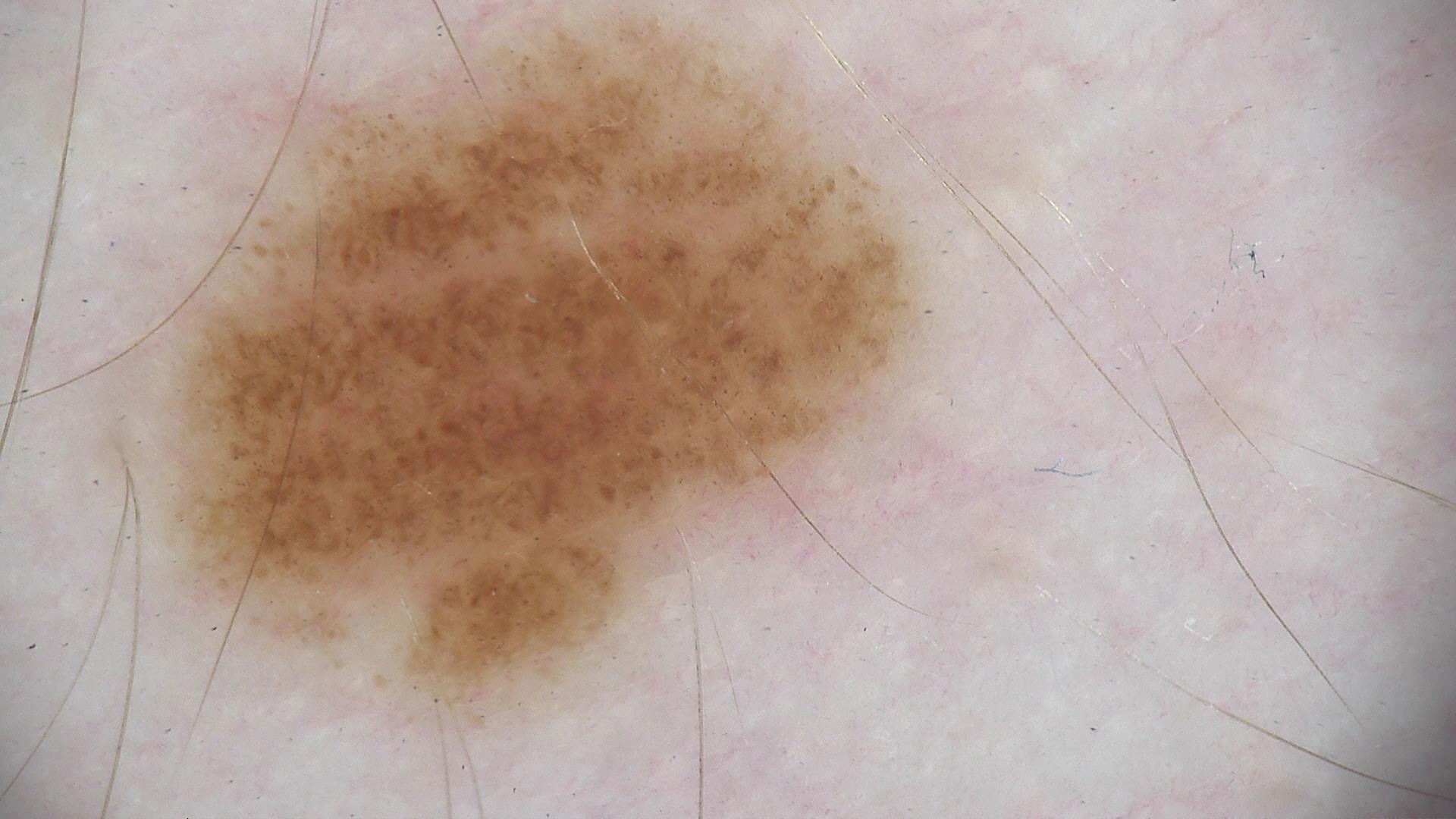{"diagnosis": {"name": "dysplastic junctional nevus", "code": "jd", "malignancy": "benign", "super_class": "melanocytic", "confirmation": "expert consensus"}}